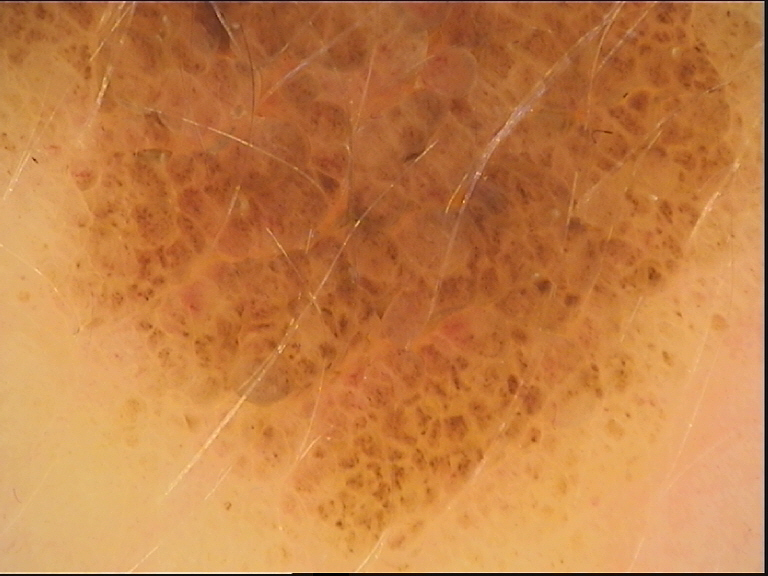Q: What is this lesion?
A: congenital compound nevus (expert consensus)